A subject in their mid-40s; a smartphone photograph of a skin lesion.
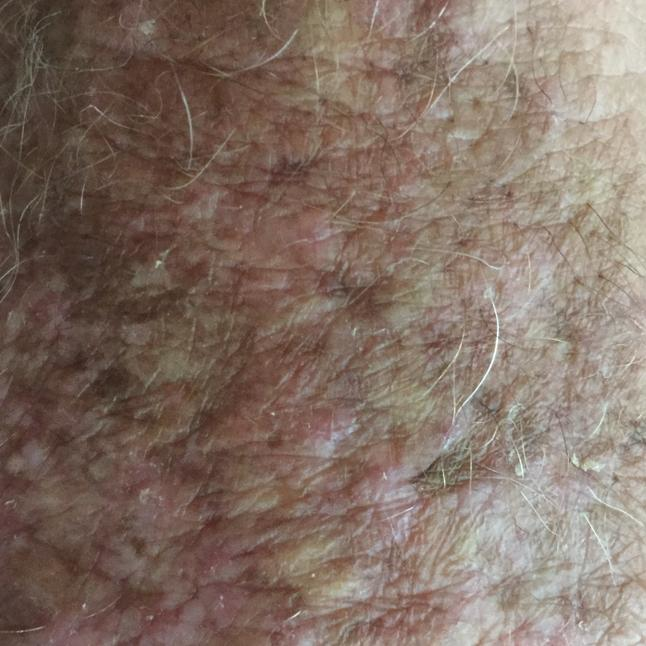The lesion involves an arm.
The patient describes that the lesion itches.
Expert review favored a premalignant lesion — an actinic keratosis.